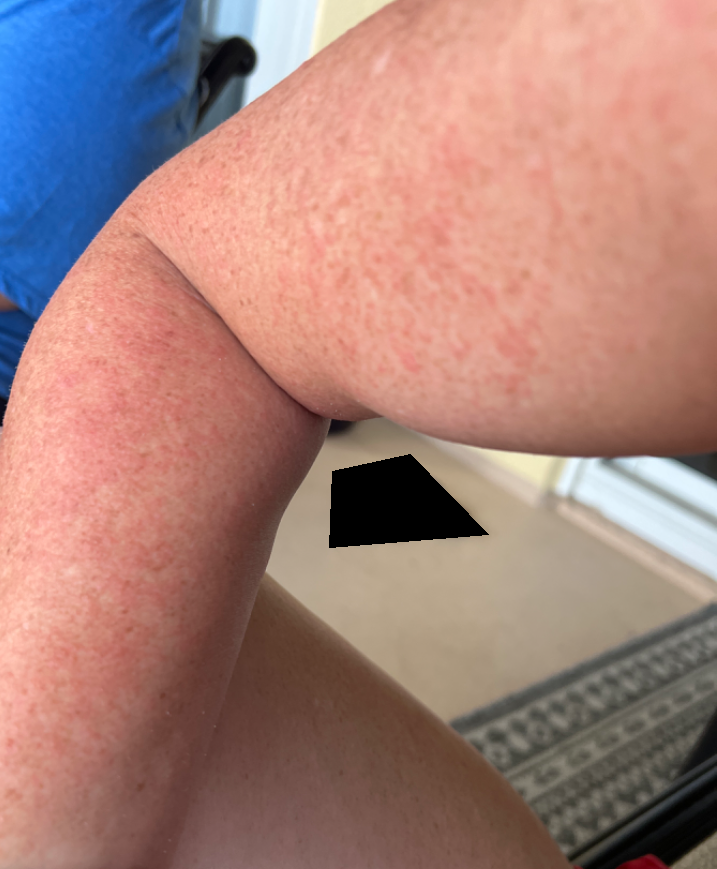Notes:
– assessment — not assessable
– symptom duration — less than one week
– site — leg and arm
– patient — female, age 30–39
– image framing — at an angle
– surface texture — raised or bumpy and fluid-filled
– patient's own categorization — skin that appeared healthy to them
– lesion symptoms — bothersome appearance